A skin lesion imaged with a dermatoscope:
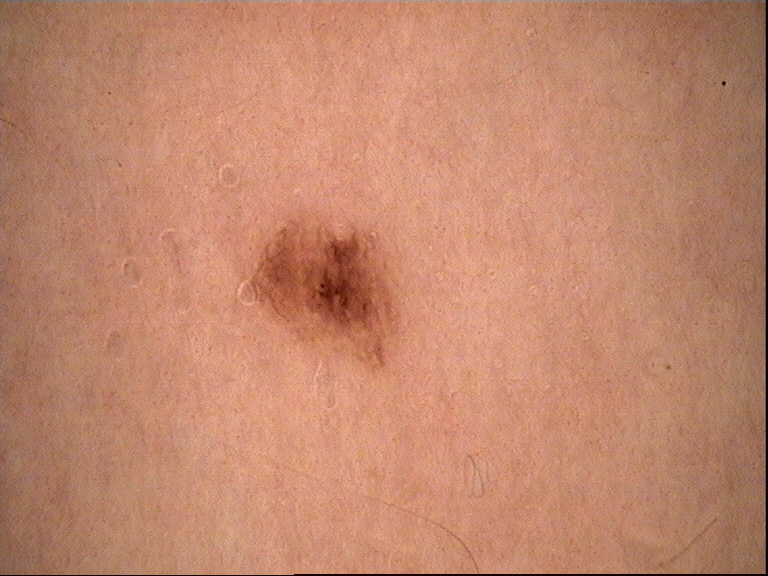diagnosis=dysplastic junctional nevus (expert consensus)